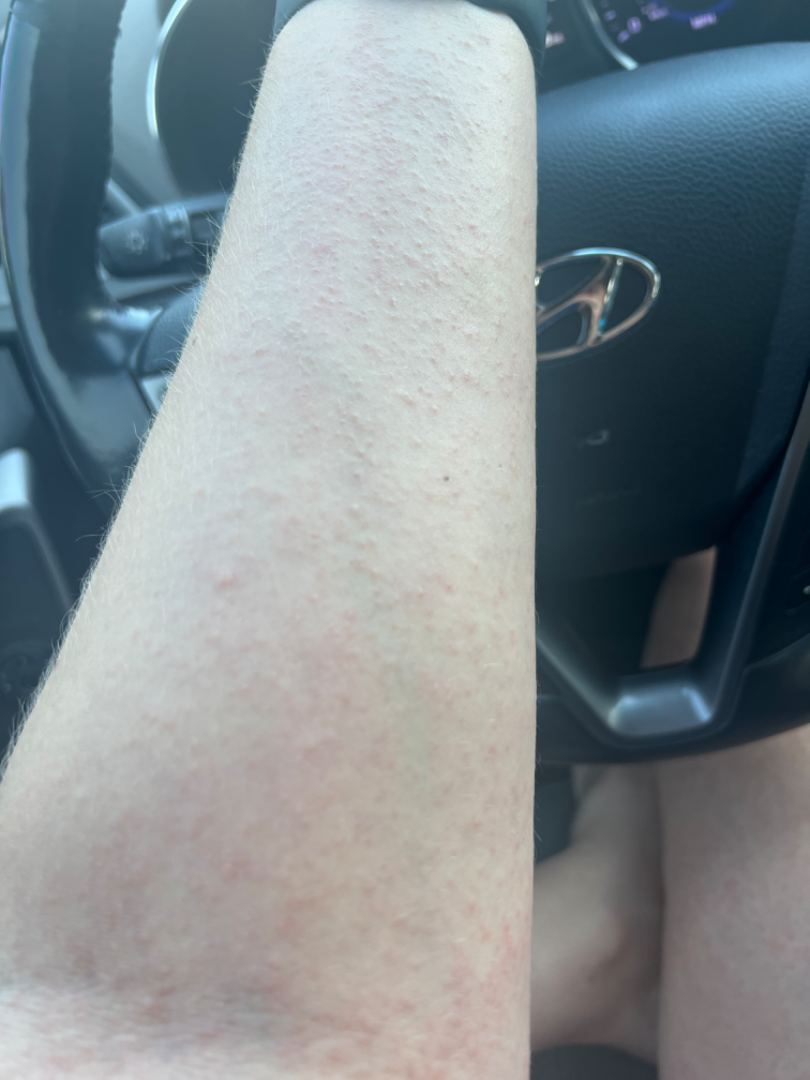On teledermatology review: favoring Miliaria; the differential also includes Eczema; also consider Photodermatitis.